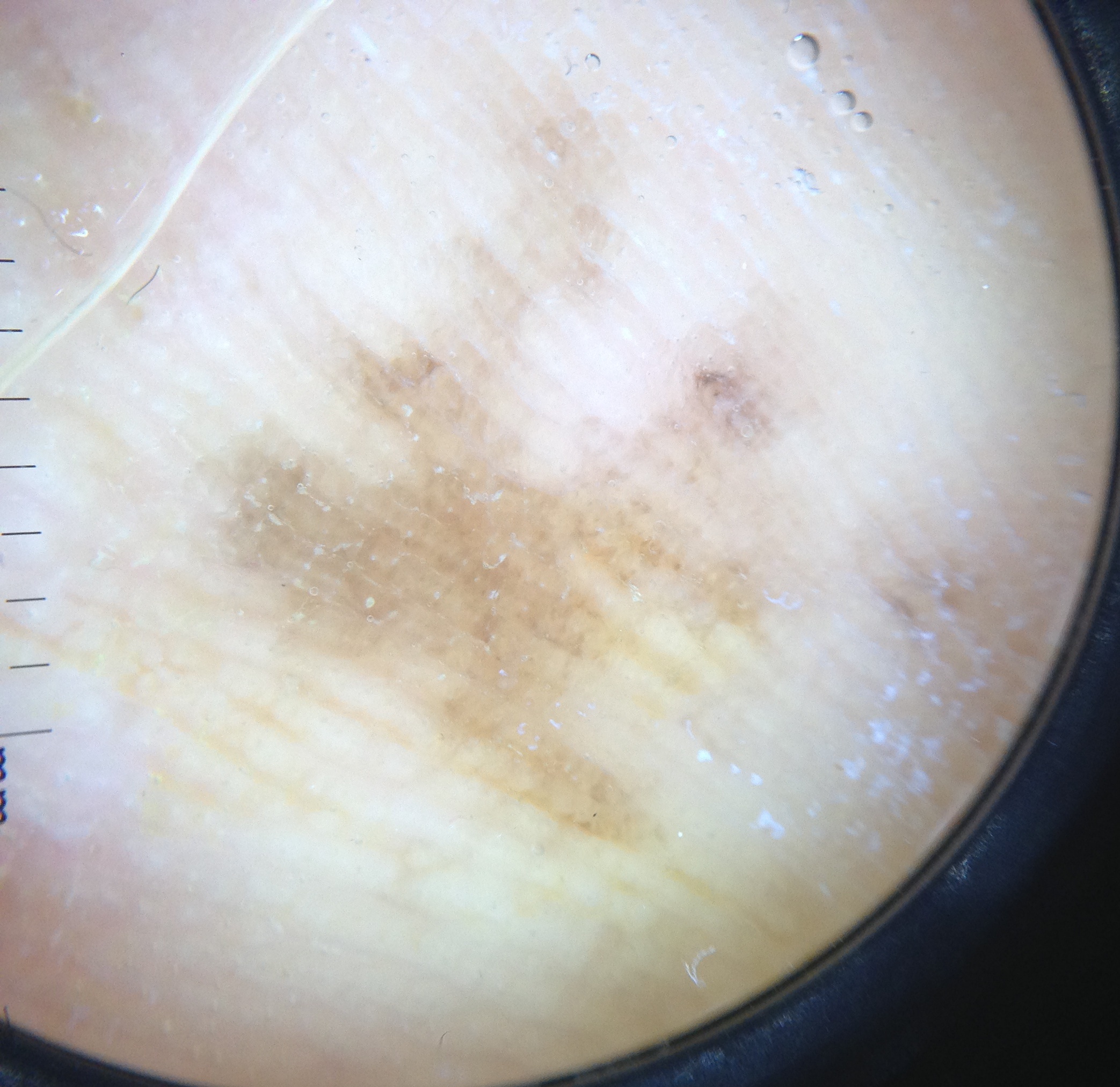The biopsy diagnosis was an acral lentiginous melanoma.